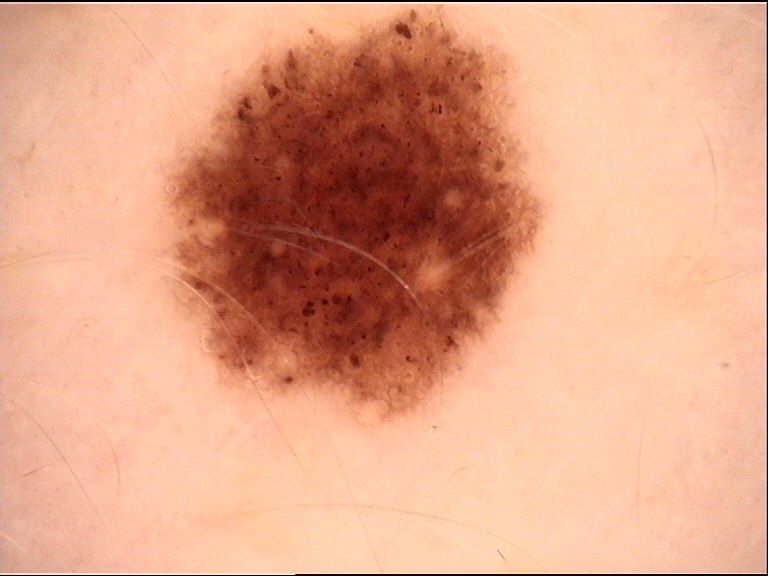Diagnosed as a junctional nevus.